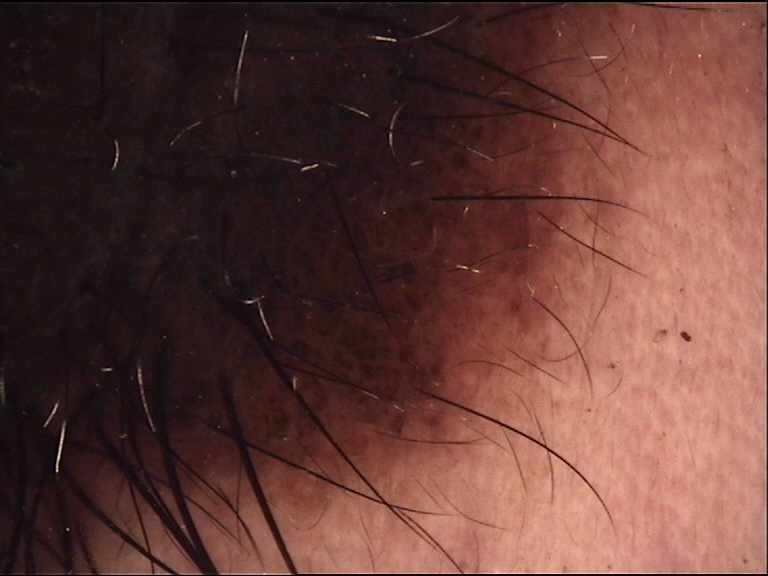<case>
  <image>dermatoscopy</image>
  <lesion_type>
    <main_class>banal</main_class>
    <pattern>compound</pattern>
  </lesion_type>
  <diagnosis>
    <name>congenital compound nevus</name>
    <code>ccb</code>
    <malignancy>benign</malignancy>
    <super_class>melanocytic</super_class>
    <confirmation>expert consensus</confirmation>
  </diagnosis>
</case>